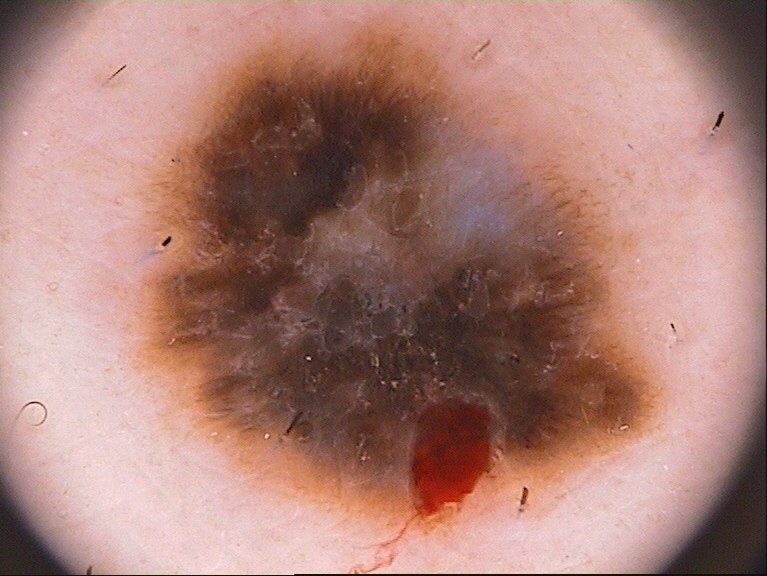This is a dermoscopic photograph of a skin lesion. The visible lesion spans x1=105 y1=6 x2=673 y2=544. The lesion takes up a large portion of the image. The clinical diagnosis was a benign lesion.